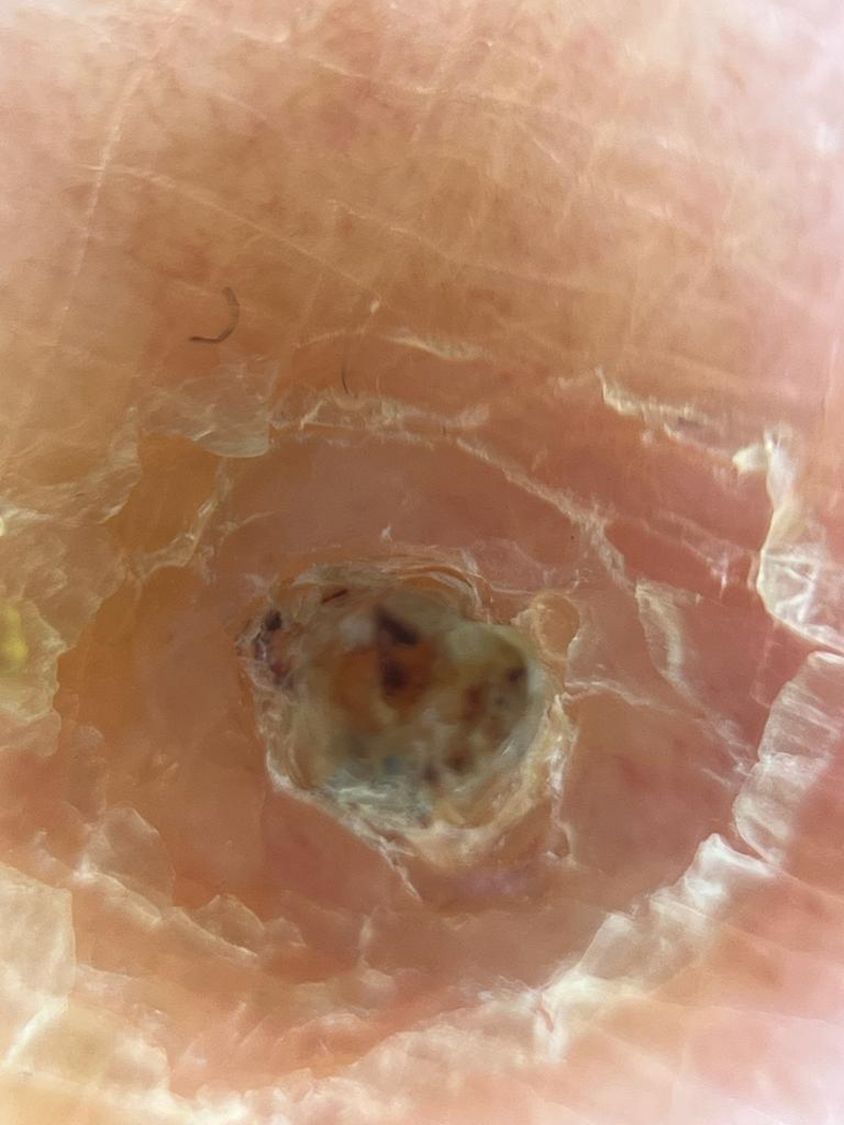A skin lesion imaged with a dermatoscope. Biopsy-confirmed as a malignant, keratinocytic lesion — a cutaneous horn.